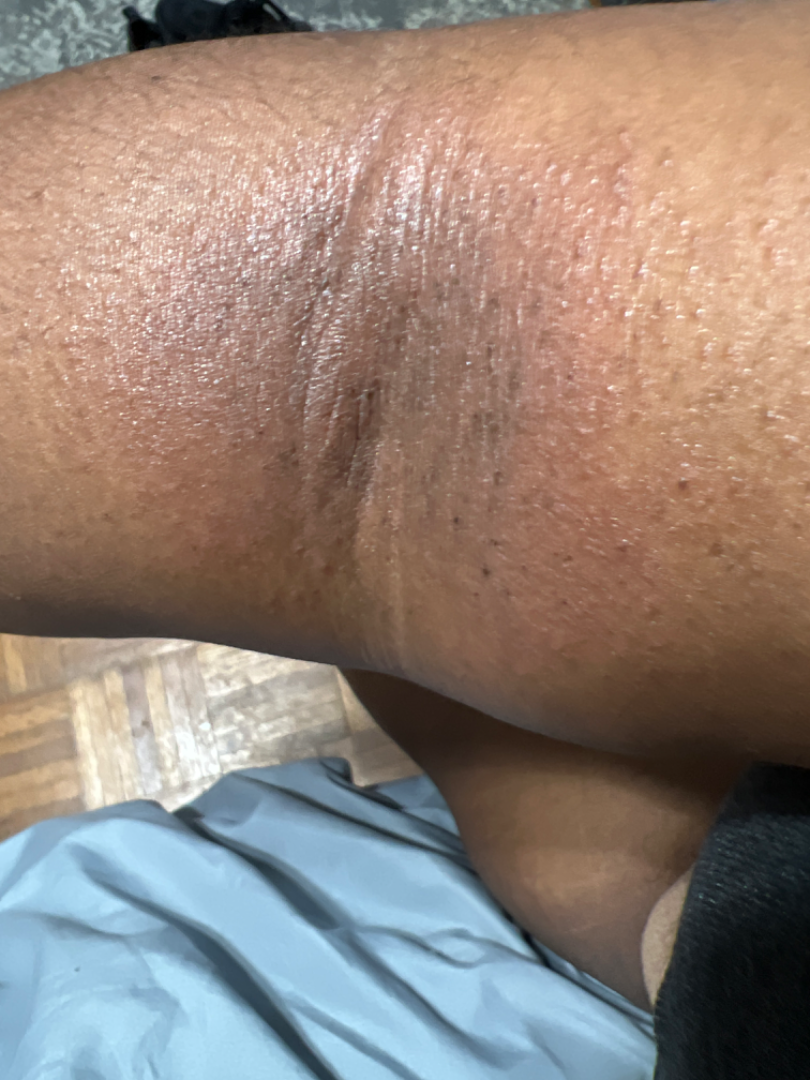Reported lesion symptoms include itching and darkening.
Present for less than one week.
Close-up view.
The patient described the issue as a rash.
The contributor reports the lesion is flat.
The lesion involves the head or neck and arm.
No associated systemic symptoms reported.
In keeping with Eczema.